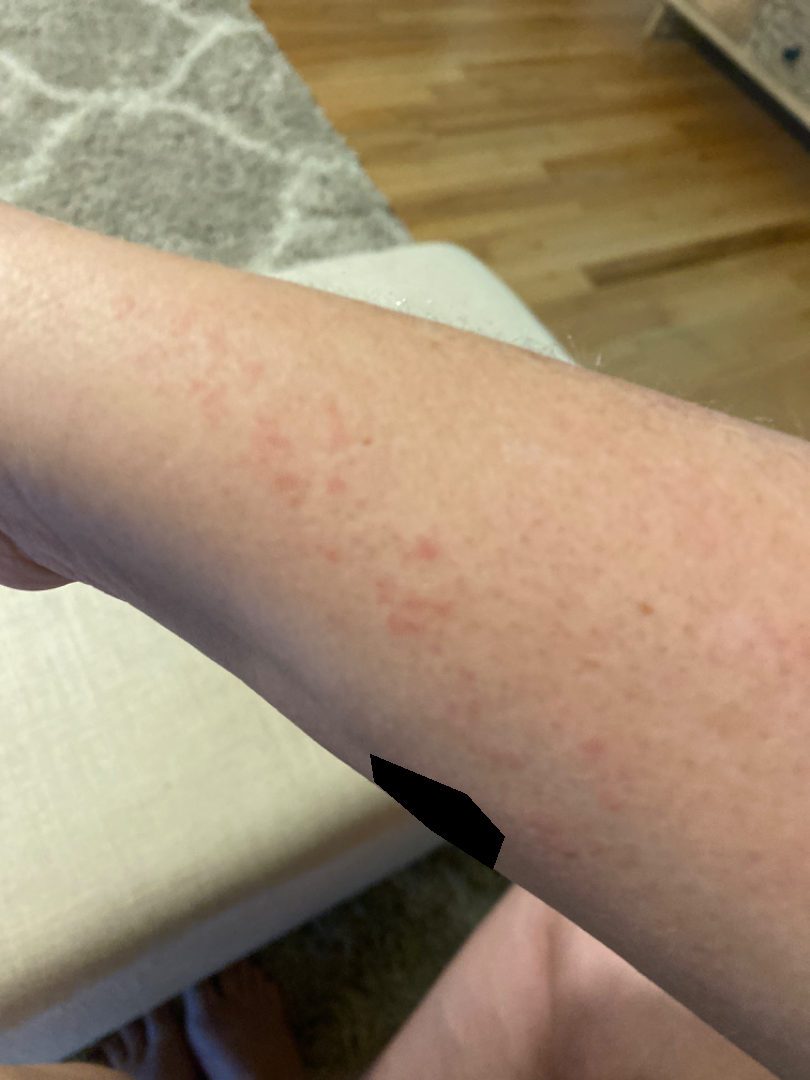History: Reported lesion symptoms include itching. Female subject, age 30–39. The lesion involves the arm. The patient reports the condition has been present for about one day. The patient reports the lesion is raised or bumpy. Skin tone: non-clinician graders estimated 3 on the MST. The patient considered this a rash. An image taken at an angle. No constitutional symptoms were reported. Impression: On photographic review by a dermatologist: Acute dermatitis, NOS (1.00).